Female patient, age 50–59 · the photo was captured at a distance · Fitzpatrick phototype II; lay reviewers estimated a Monk skin tone scale of 2 · reported lesion symptoms include itching and enlargement · the lesion involves the arm · the patient reports associated fatigue · reported duration is one to four weeks.
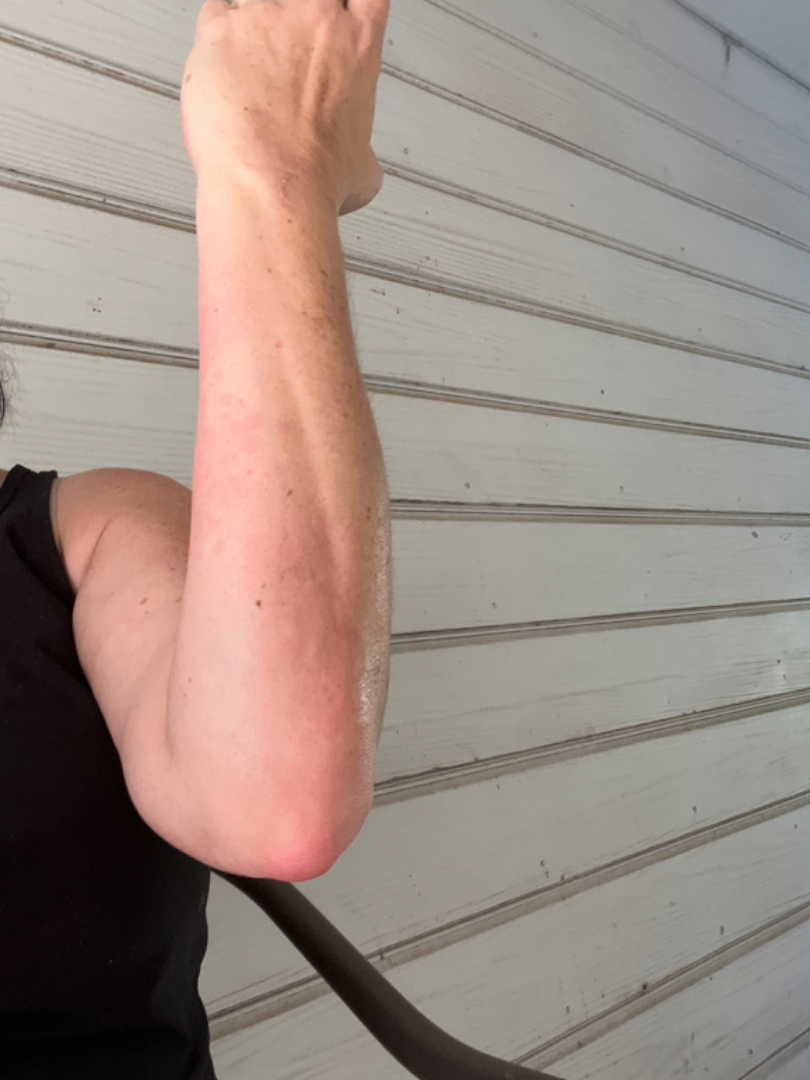* assessment · Urticaria (possible); Eczema (possible); Allergic Contact Dermatitis (possible)